A dermoscopic image of a skin lesion.
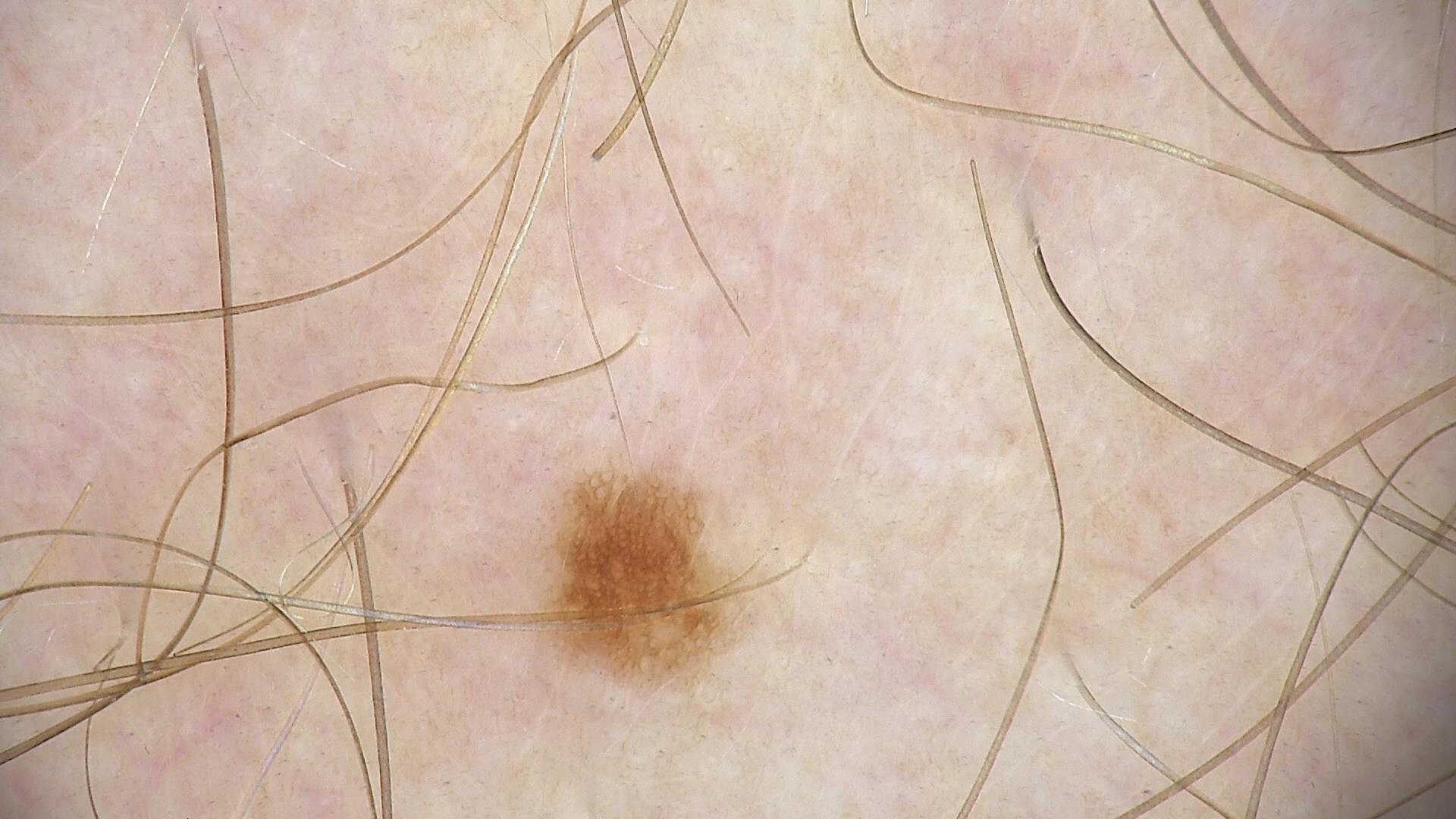Classified as a dysplastic junctional nevus.